The lesion involves the sole of the foot, leg and front of the torso; this is a close-up image; female contributor, age 50–59 — 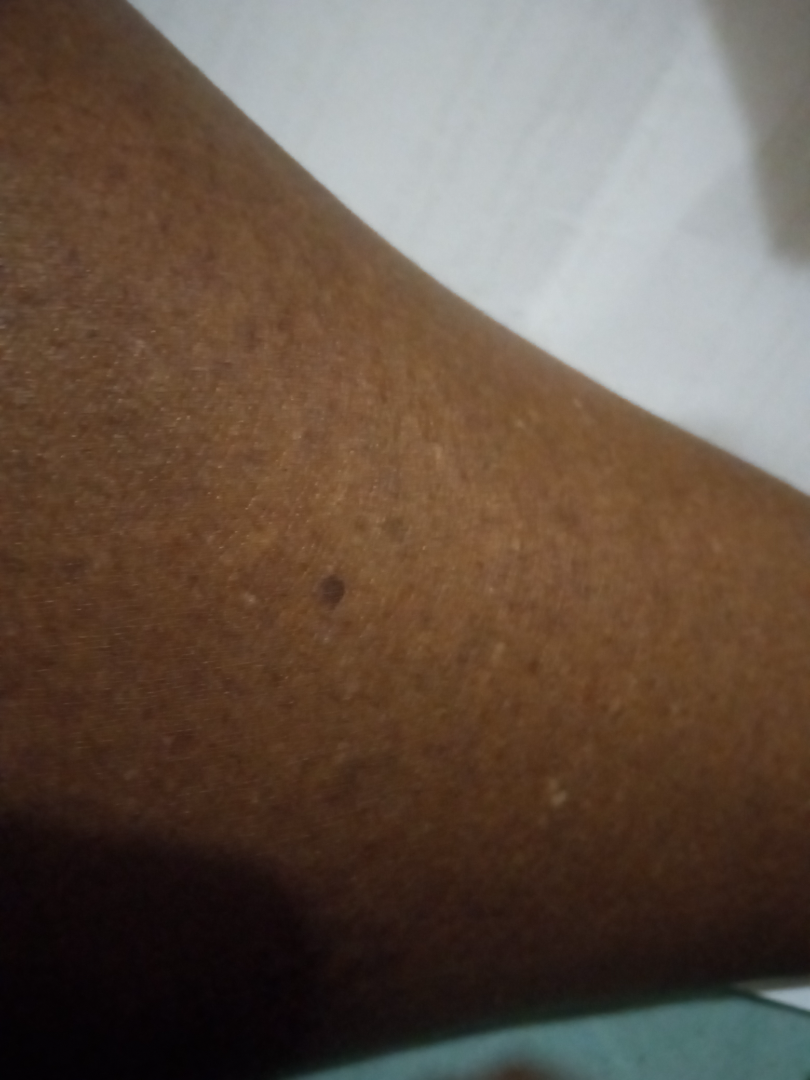Case summary:
– assessment: no skin condition identified